Female contributor, age 30–39; the photograph was taken at a distance.
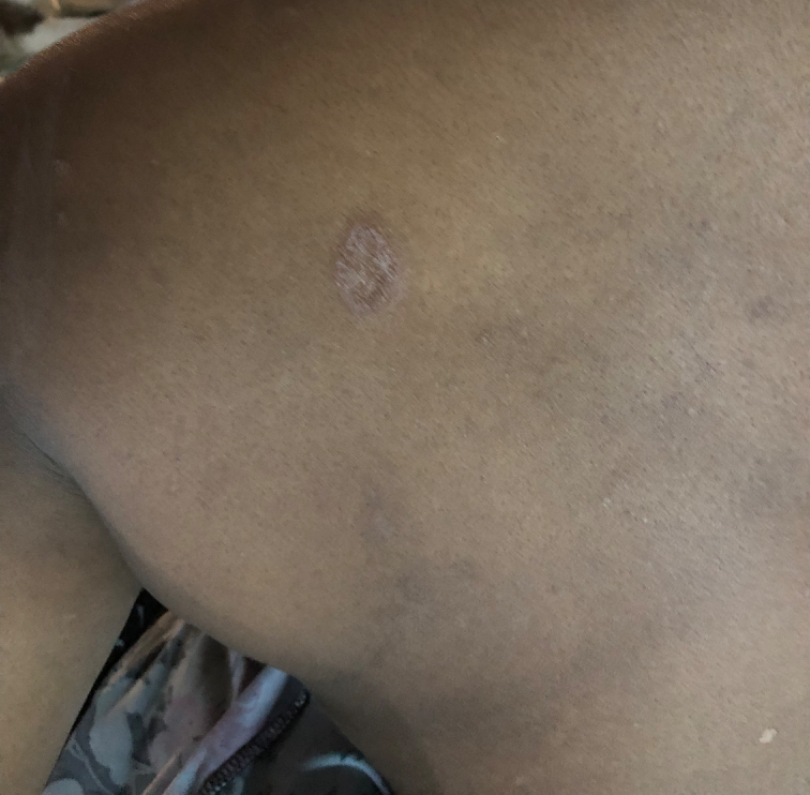Three independent reviewers: favoring Tinea; also consider Deep fungal infection; also raised was SCC/SCCIS; a more distant consideration is Tuberculosis of skin and subcutaneous tissue.